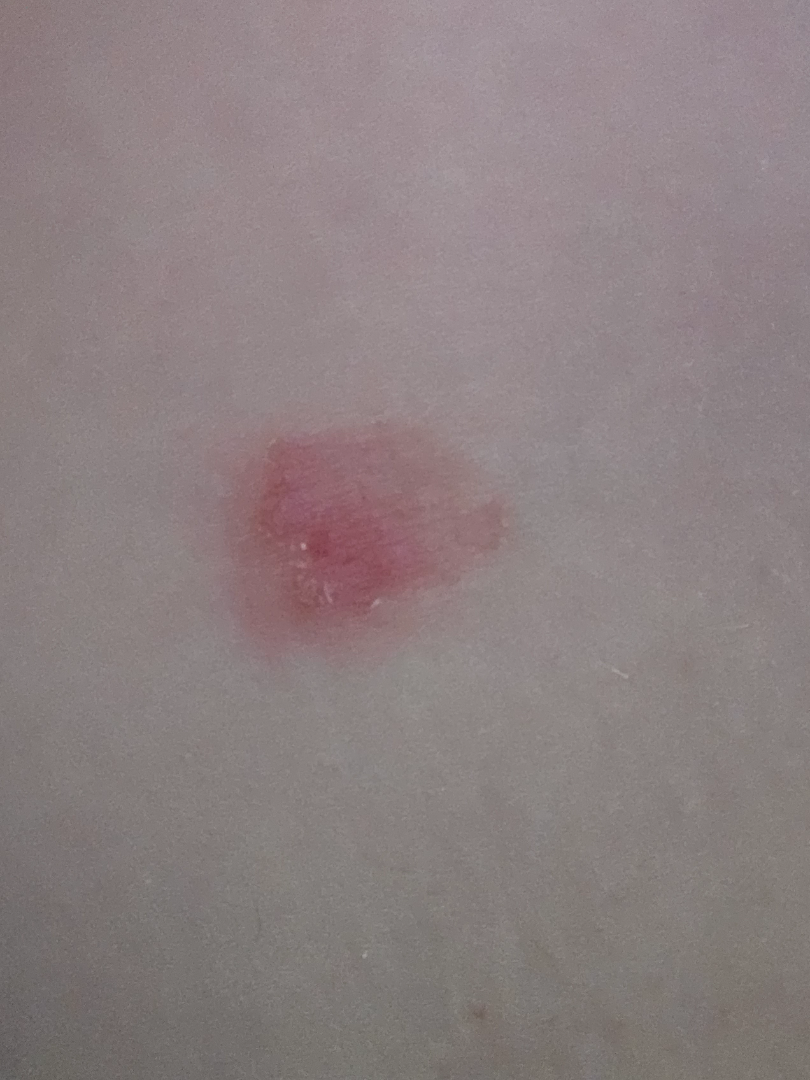Notes:
– assessment · indeterminate from the photograph
– view · close-up